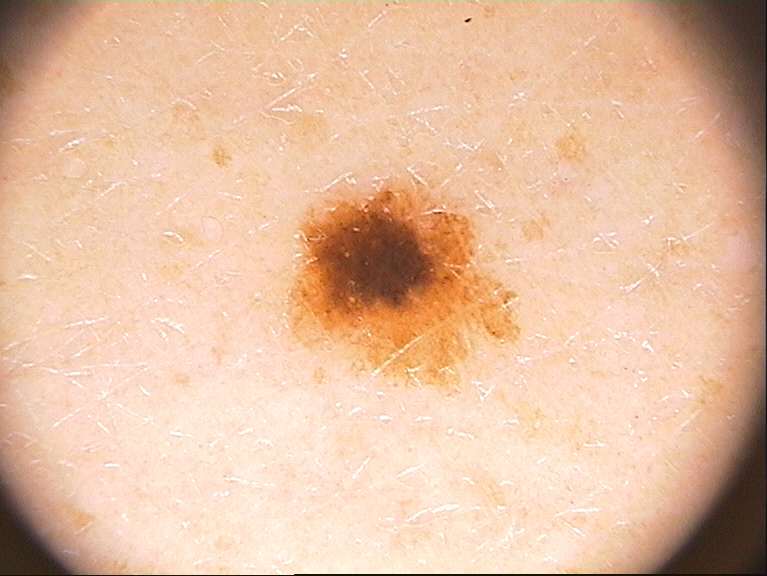A female patient, roughly 40 years of age.
A skin lesion imaged with a dermatoscope.
In (x1, y1, x2, y2) order, lesion location: [271,170,521,395].
On dermoscopy, the lesion shows pigment network; no globules, streaks, milia-like cysts, or negative network.
The clinical diagnosis was a melanocytic nevus.